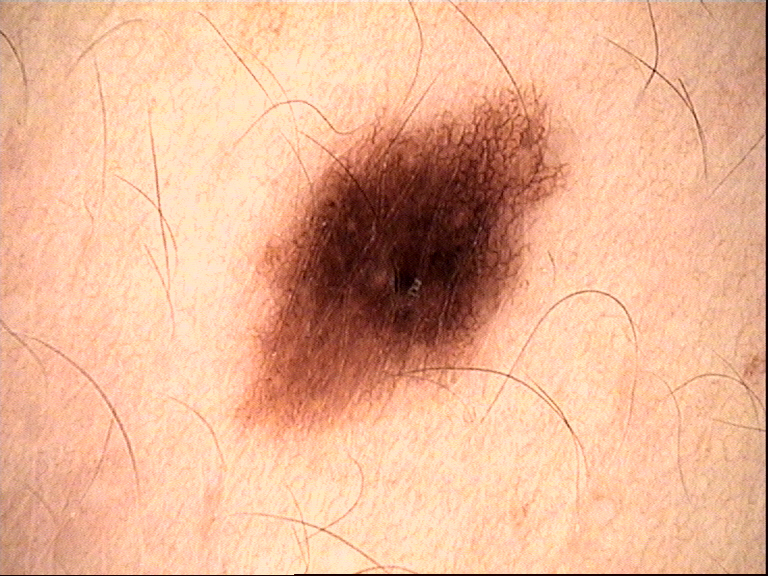A dermoscopic photograph of a skin lesion. Diagnosed as a dysplastic junctional nevus.